A dermoscopic close-up of a skin lesion:
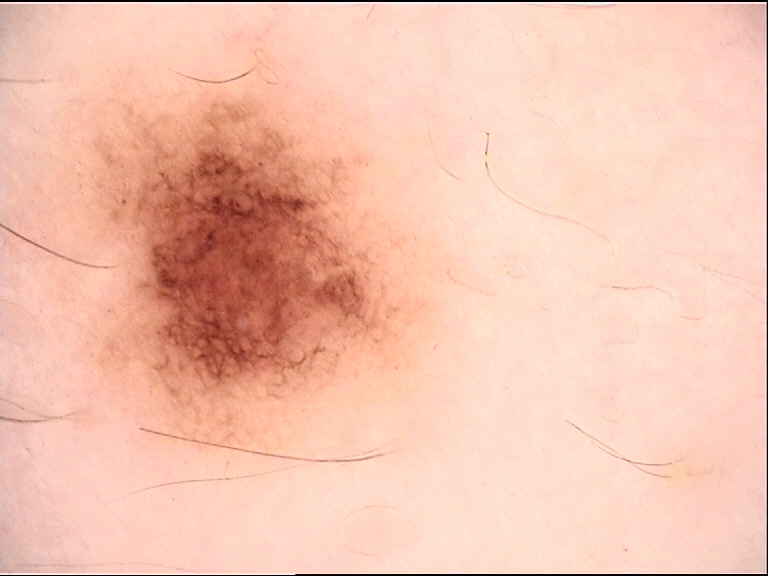Findings:
- diagnostic label · dysplastic junctional nevus (expert consensus)